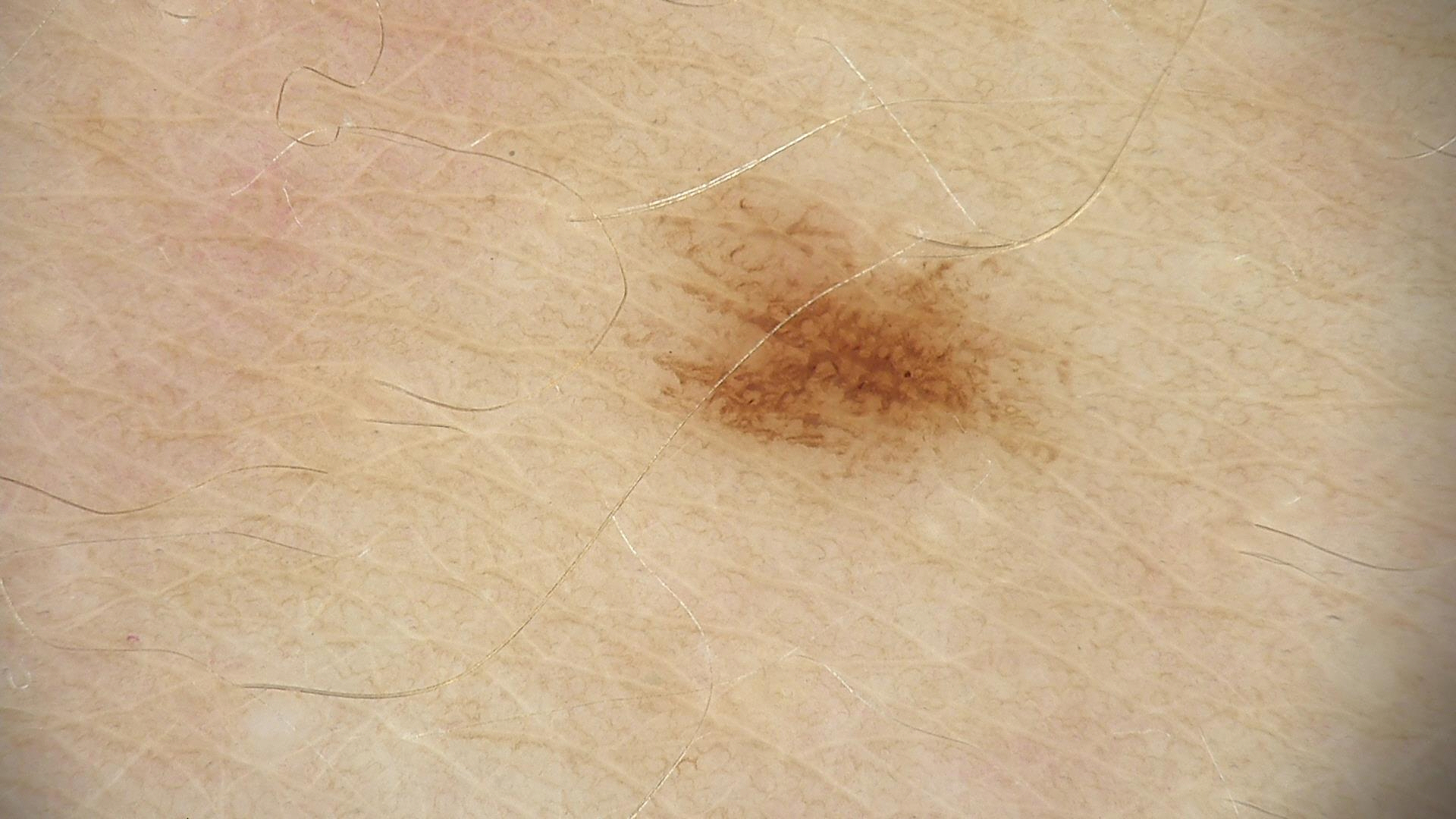Q: What was the diagnostic impression?
A: dysplastic junctional nevus (expert consensus)